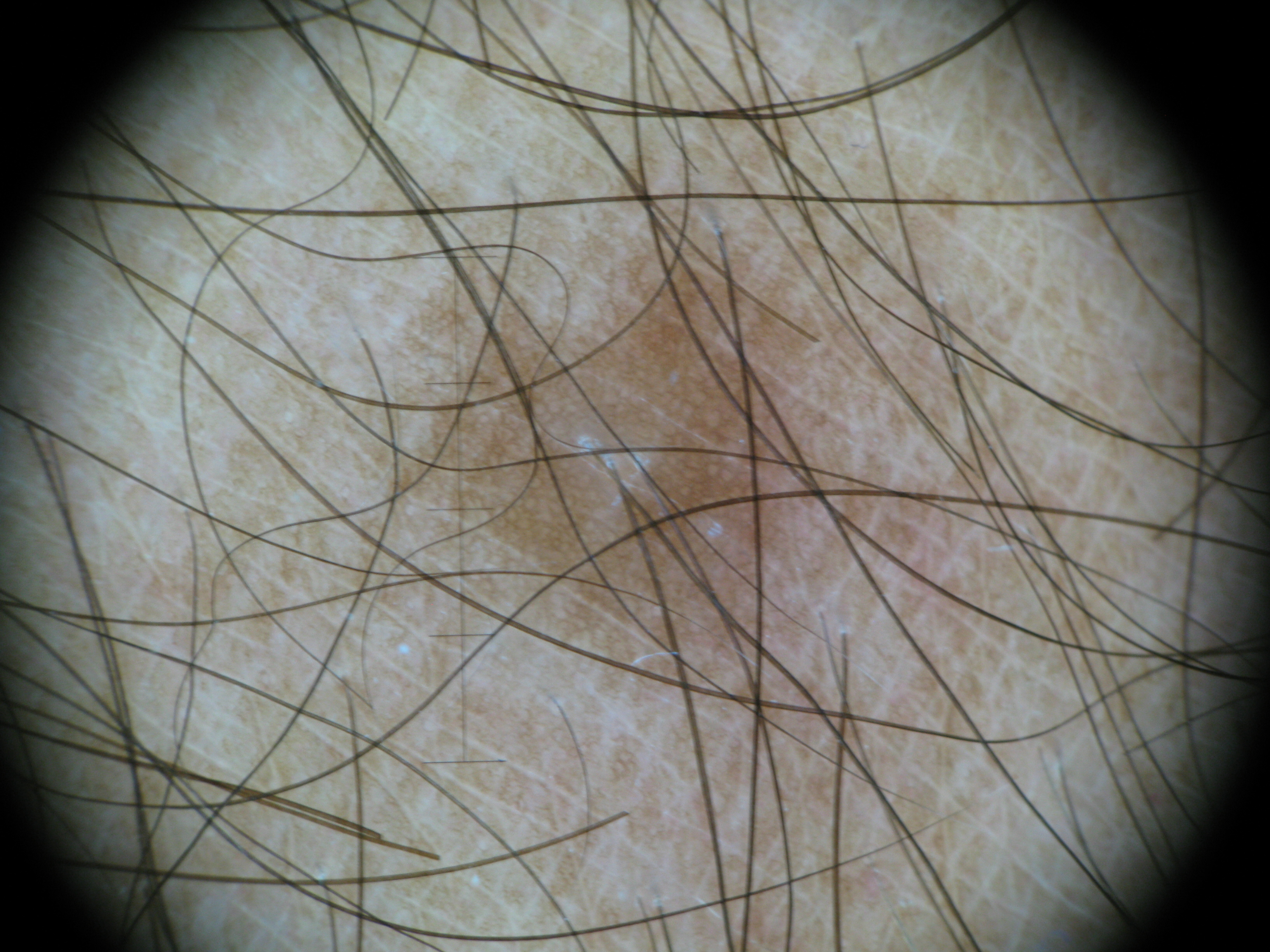image type: dermatoscopy; diagnosis: dermatofibroma (expert consensus).